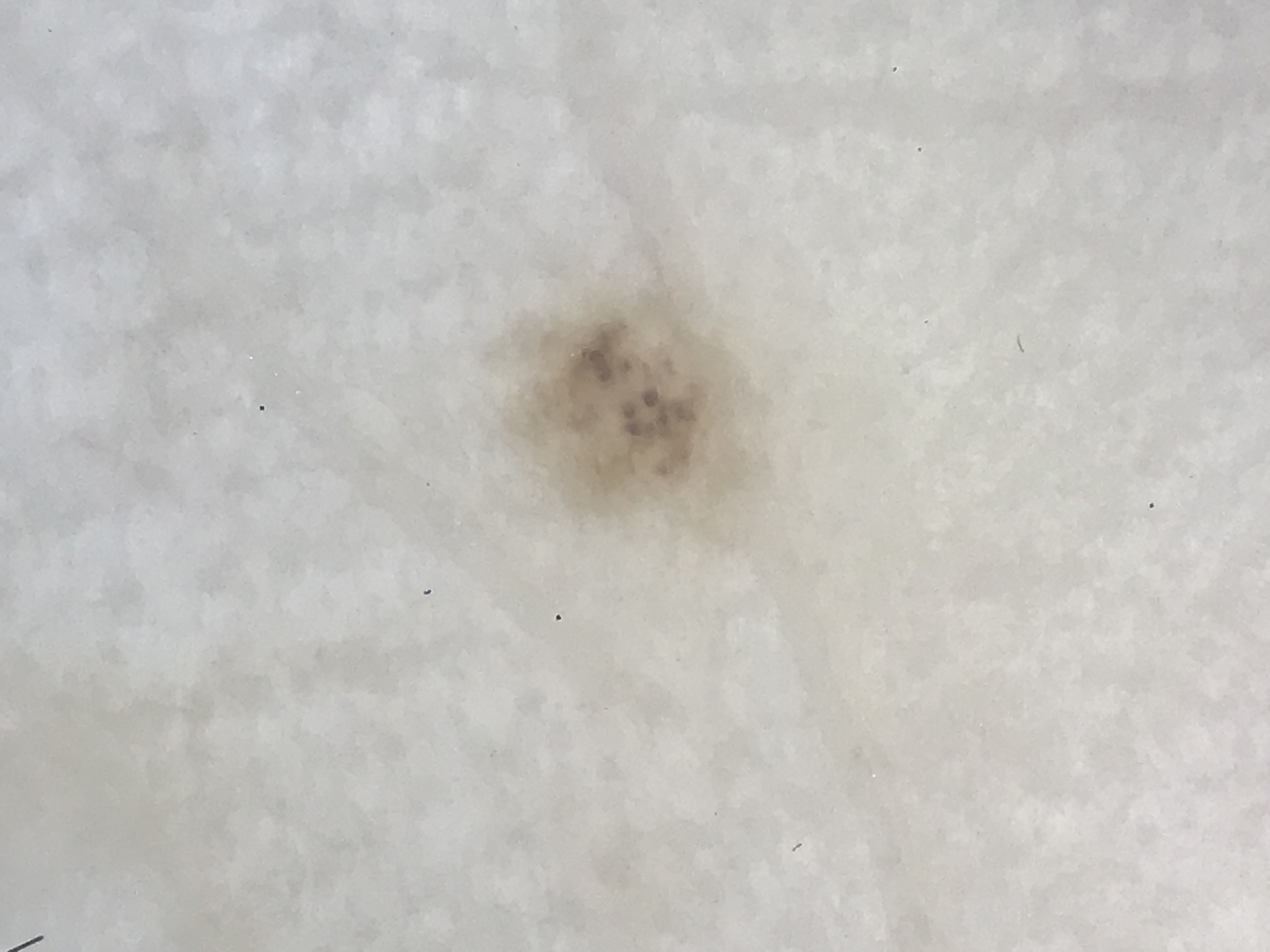assessment = acral junctional nevus (expert consensus).